Recorded as Fitzpatrick phototype II; a dermoscopic photograph of a skin lesion — 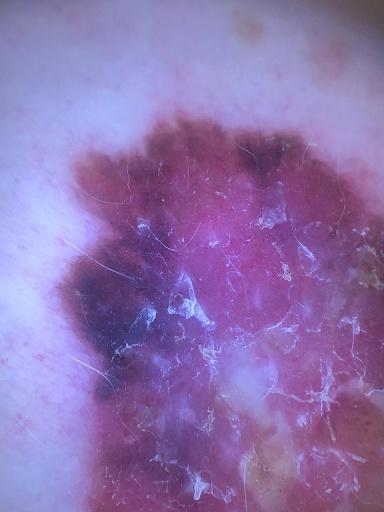Image and clinical context: The lesion is on a lower extremity. Diagnosis: Histopathological examination showed a melanoma.